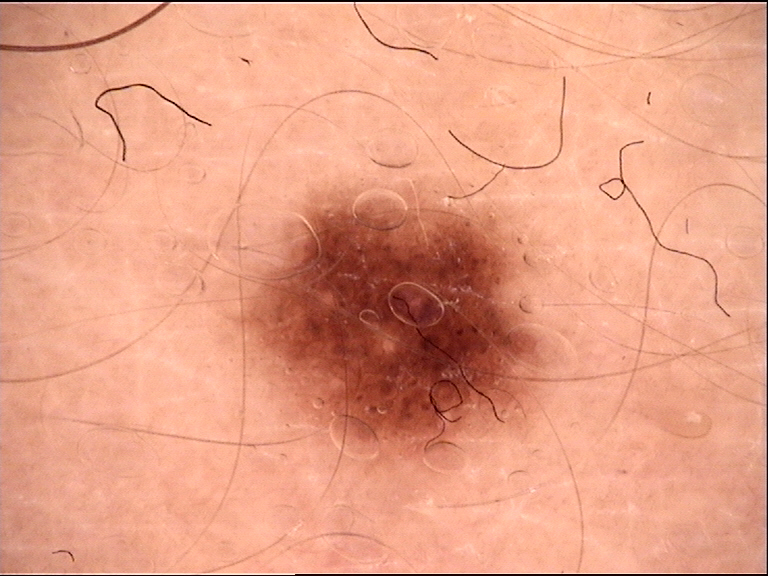A dermoscopic photograph of a skin lesion.
Diagnosed as a banal lesion — a junctional nevus.